The photograph is a close-up of the affected area — 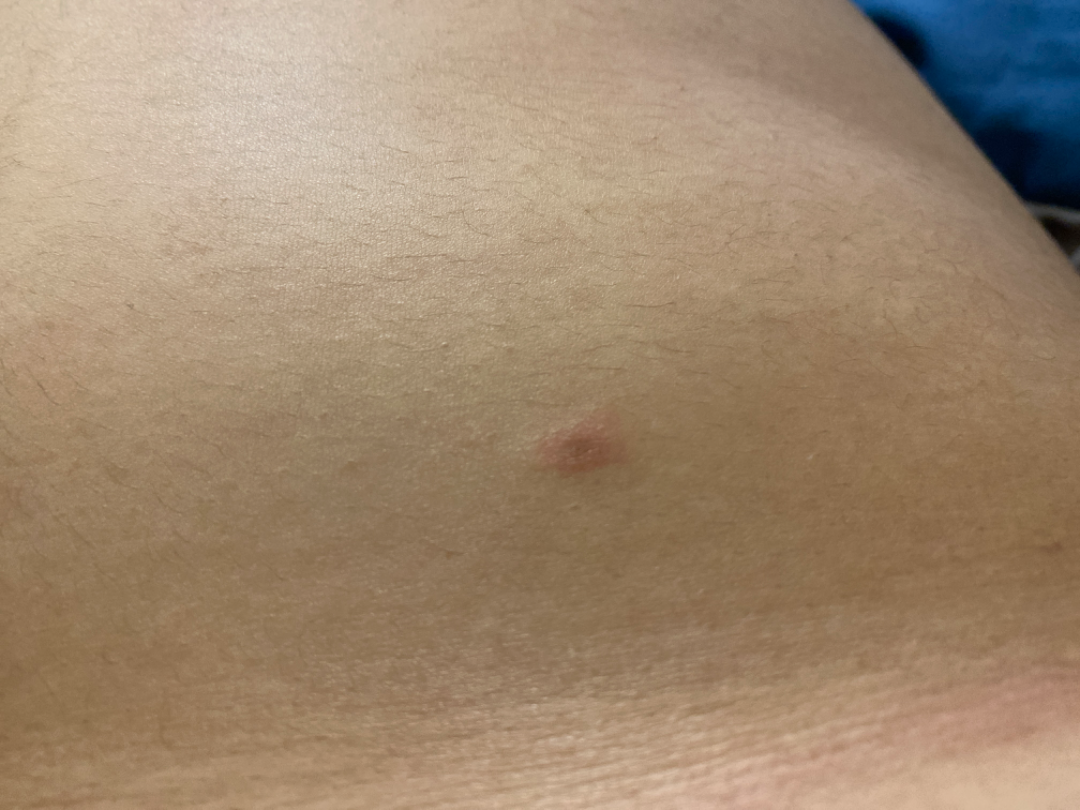assessment: indeterminate